A patient in their 30s; a clinical photograph showing a skin lesion — 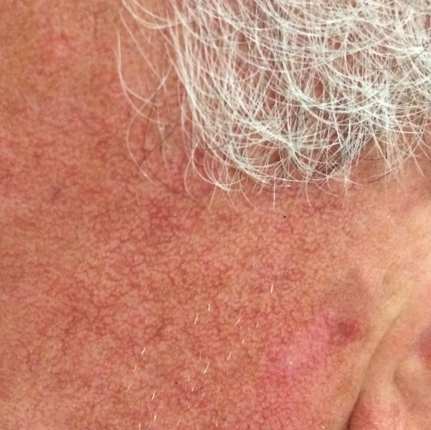Case summary:
The lesion is on the face. No symptoms reported.
Conclusion:
Diagnosed by dermatologist consensus as an actinic keratosis.